A clinical close-up of a skin lesion. A male patient age 83 — 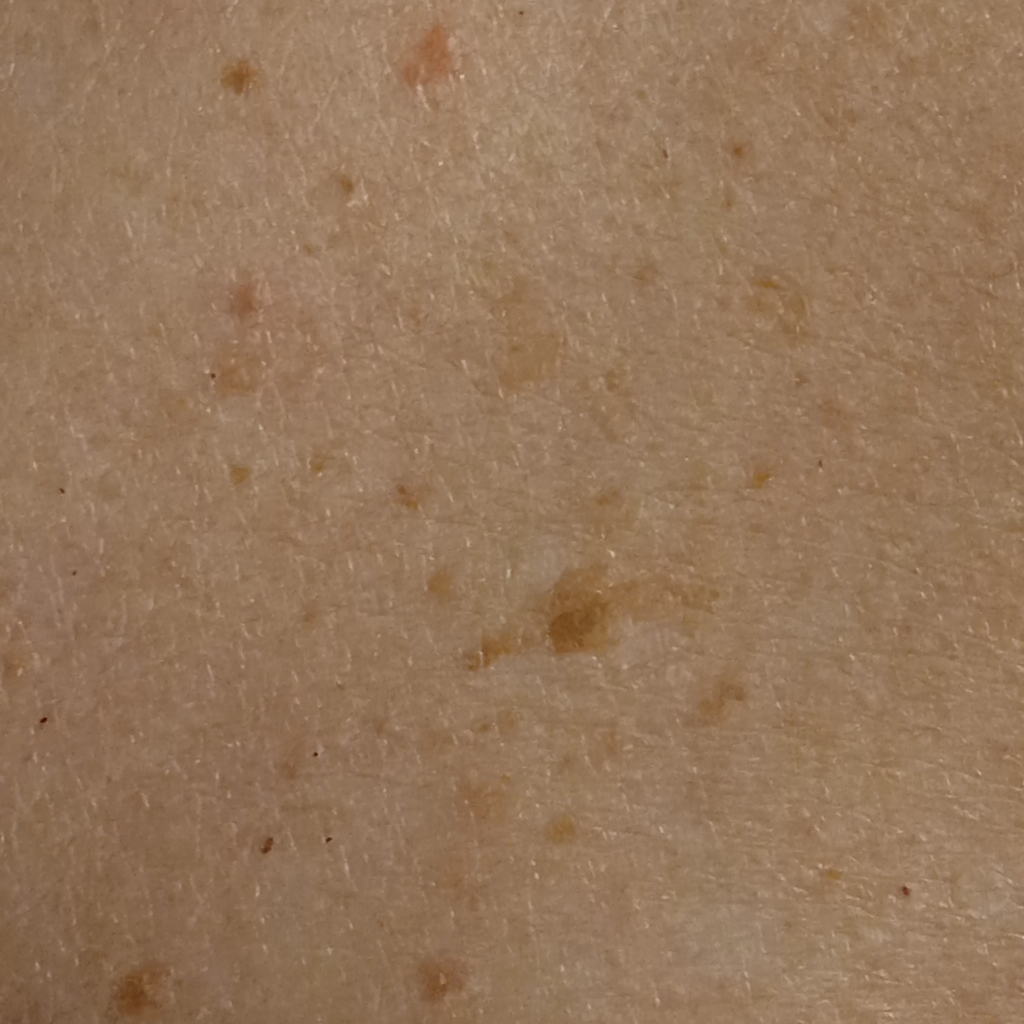- body site · the back
- assessment · seborrheic keratosis (dermatologist consensus)